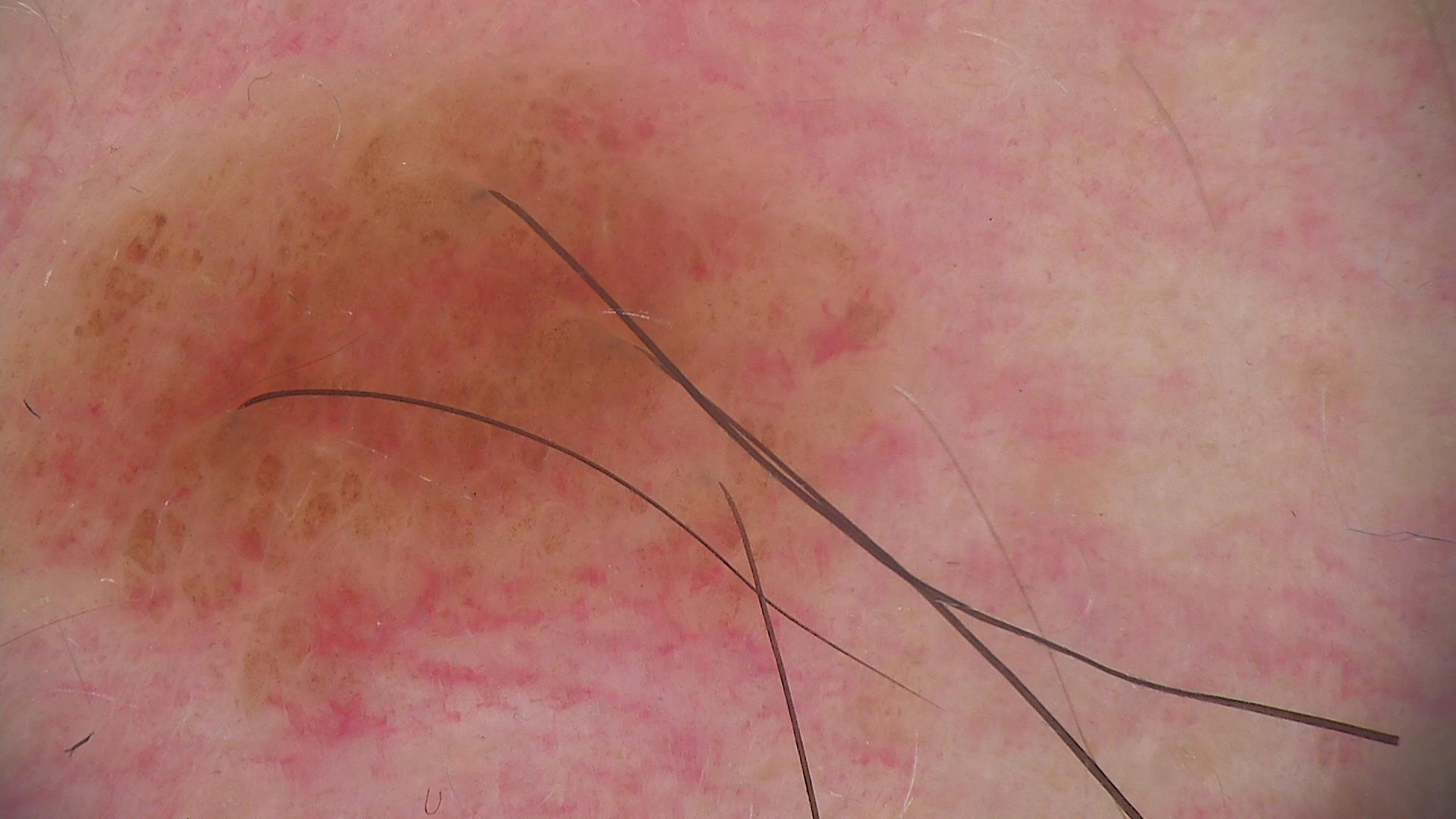Case:
The morphology is that of a banal lesion.
Conclusion:
The diagnostic label was a compound nevus.